The lesion involves the leg, top or side of the foot, front of the torso, back of the torso, head or neck and arm; the subject is a female aged 30–39; this is a close-up image — 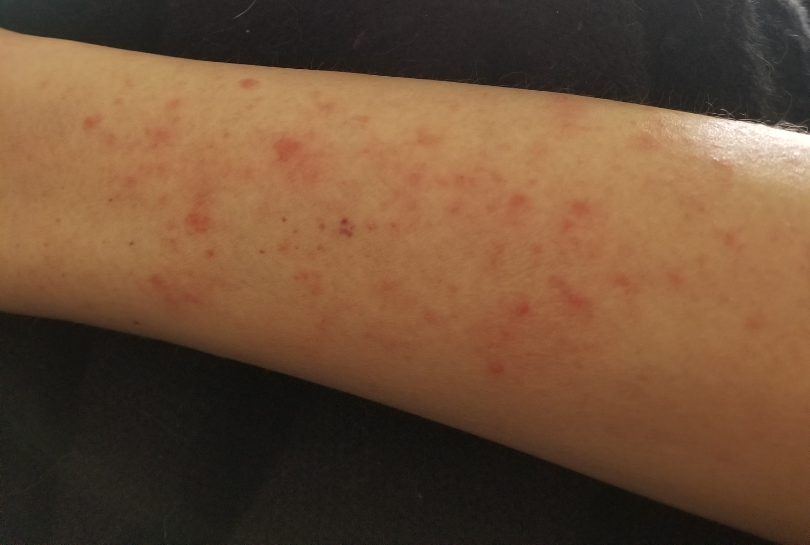Q: Could the case be diagnosed?
A: ungradable on photographic review
Q: Patient's own categorization?
A: a rash
Q: How long has this been present?
A: three to twelve months
Q: What is the patient's skin tone?
A: FST III
Q: Reported symptoms?
A: burning, itching, bleeding, pain and enlargement
Q: Any systemic symptoms?
A: none reported